A dermoscopic close-up of a skin lesion.
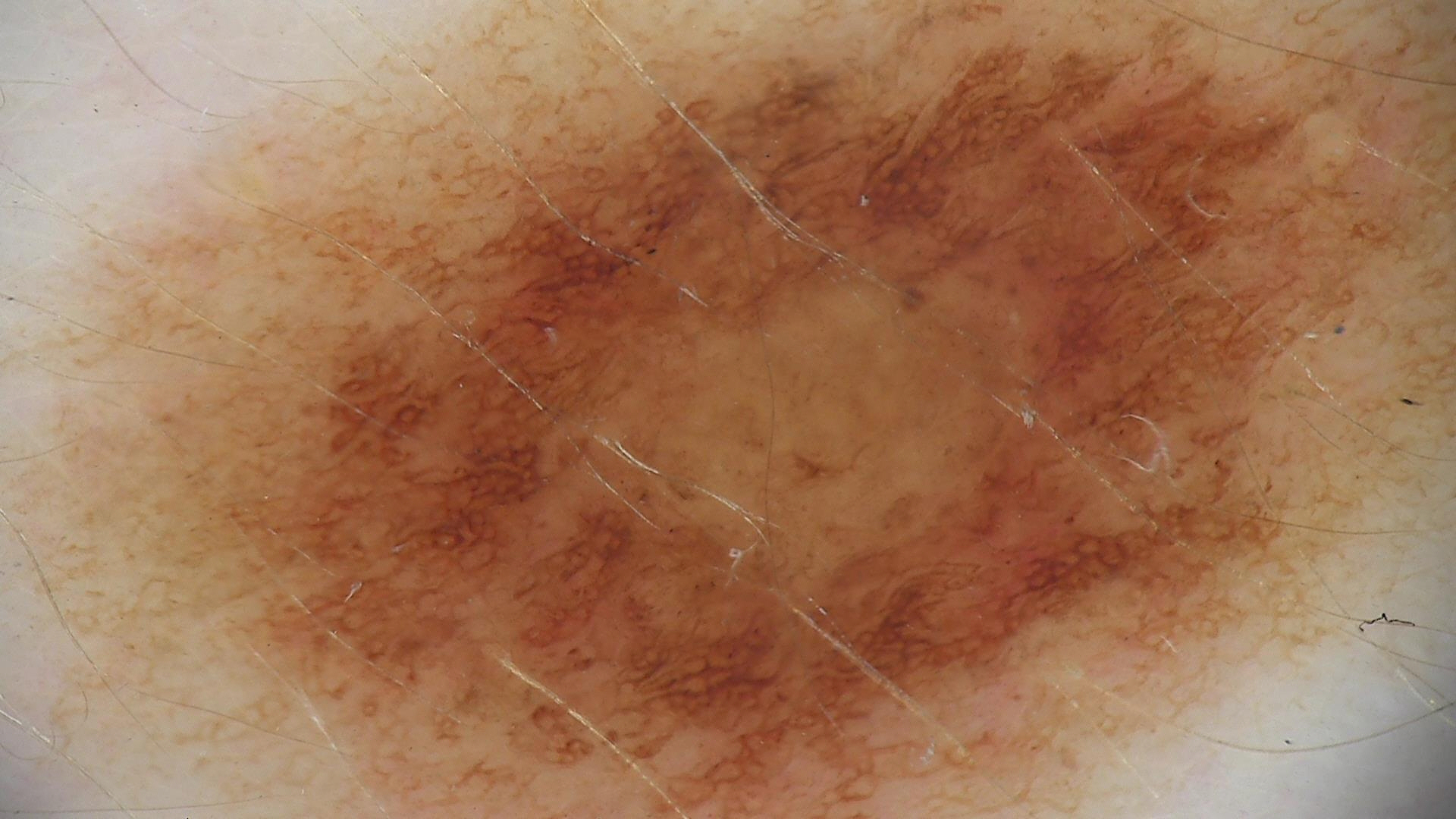{
  "diagnosis": {
    "name": "dysplastic junctional nevus",
    "code": "jd",
    "malignancy": "benign",
    "super_class": "melanocytic",
    "confirmation": "expert consensus"
  }
}